A dermoscopy image of a single skin lesion:
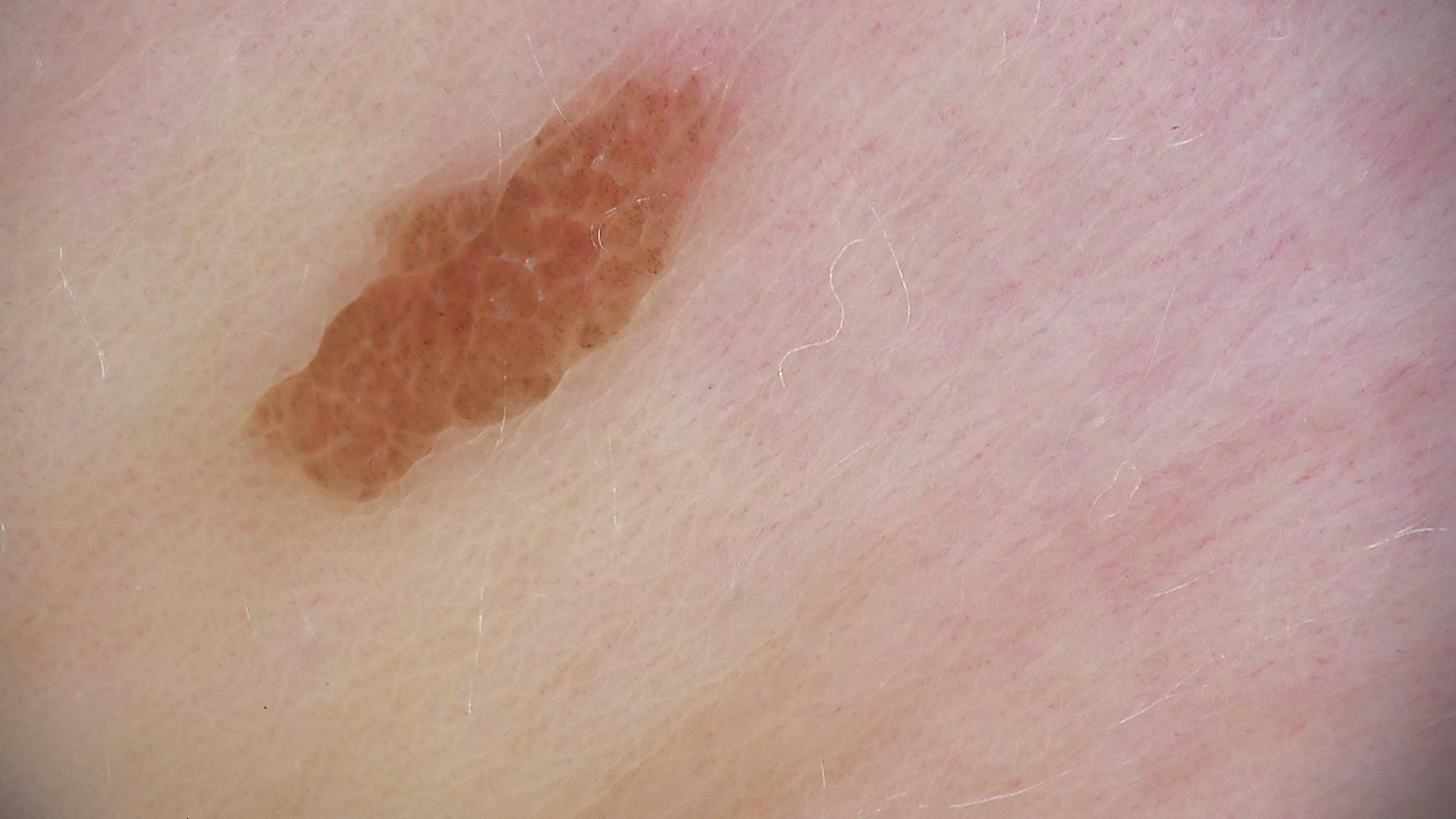<lesion>
<diagnosis>
<name>compound nevus</name>
<code>cb</code>
<malignancy>benign</malignancy>
<super_class>melanocytic</super_class>
<confirmation>expert consensus</confirmation>
</diagnosis>
</lesion>